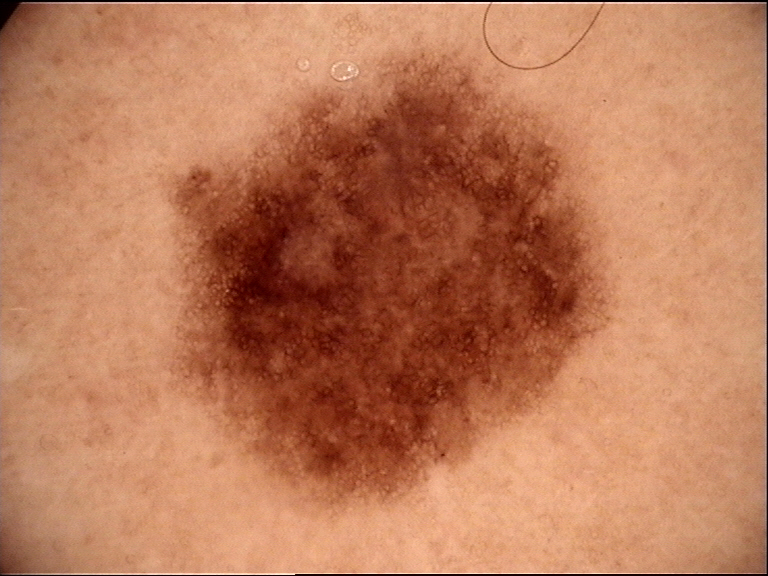Classified as a benign lesion — a dysplastic junctional nevus.